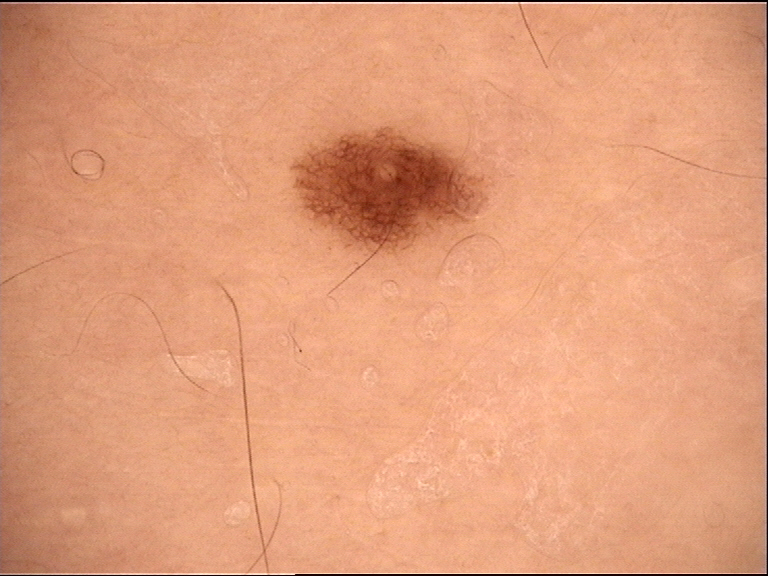A dermoscopic photograph of a skin lesion. Labeled as a dysplastic junctional nevus.